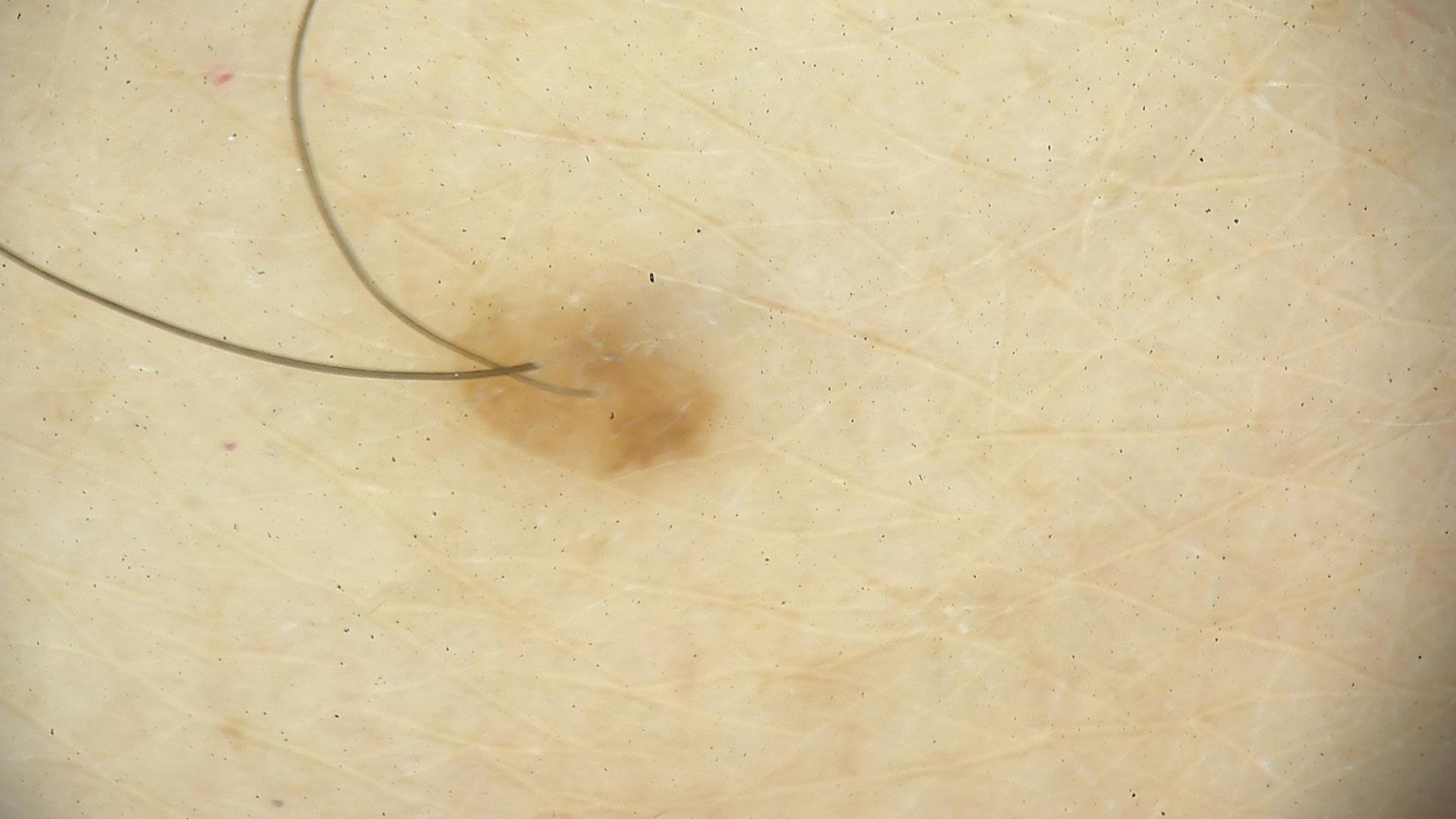| feature | finding |
|---|---|
| assessment | dermal nevus (expert consensus) |